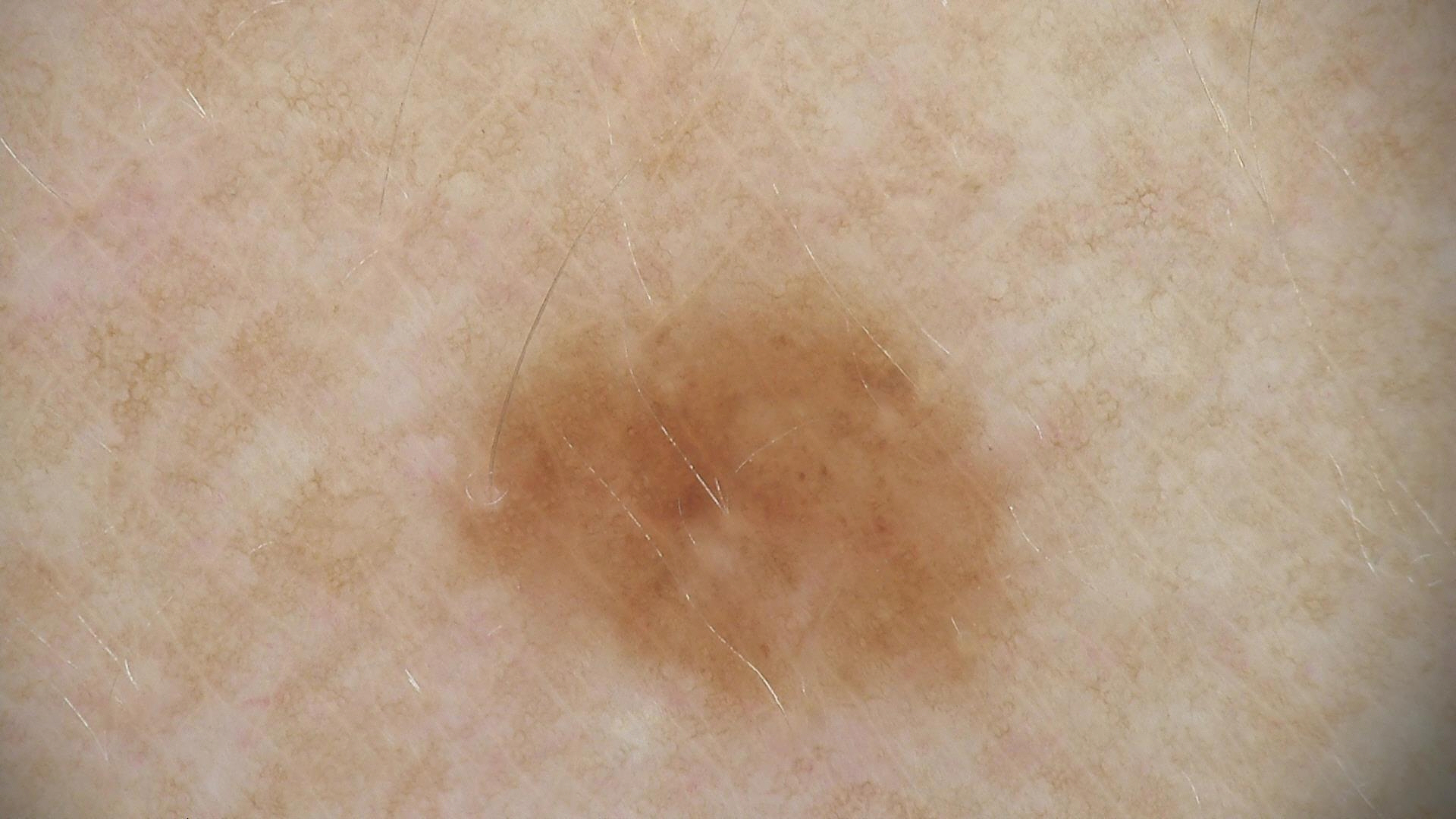Impression:
The diagnosis was a dysplastic junctional nevus.